A dermatoscopic image of a skin lesion:
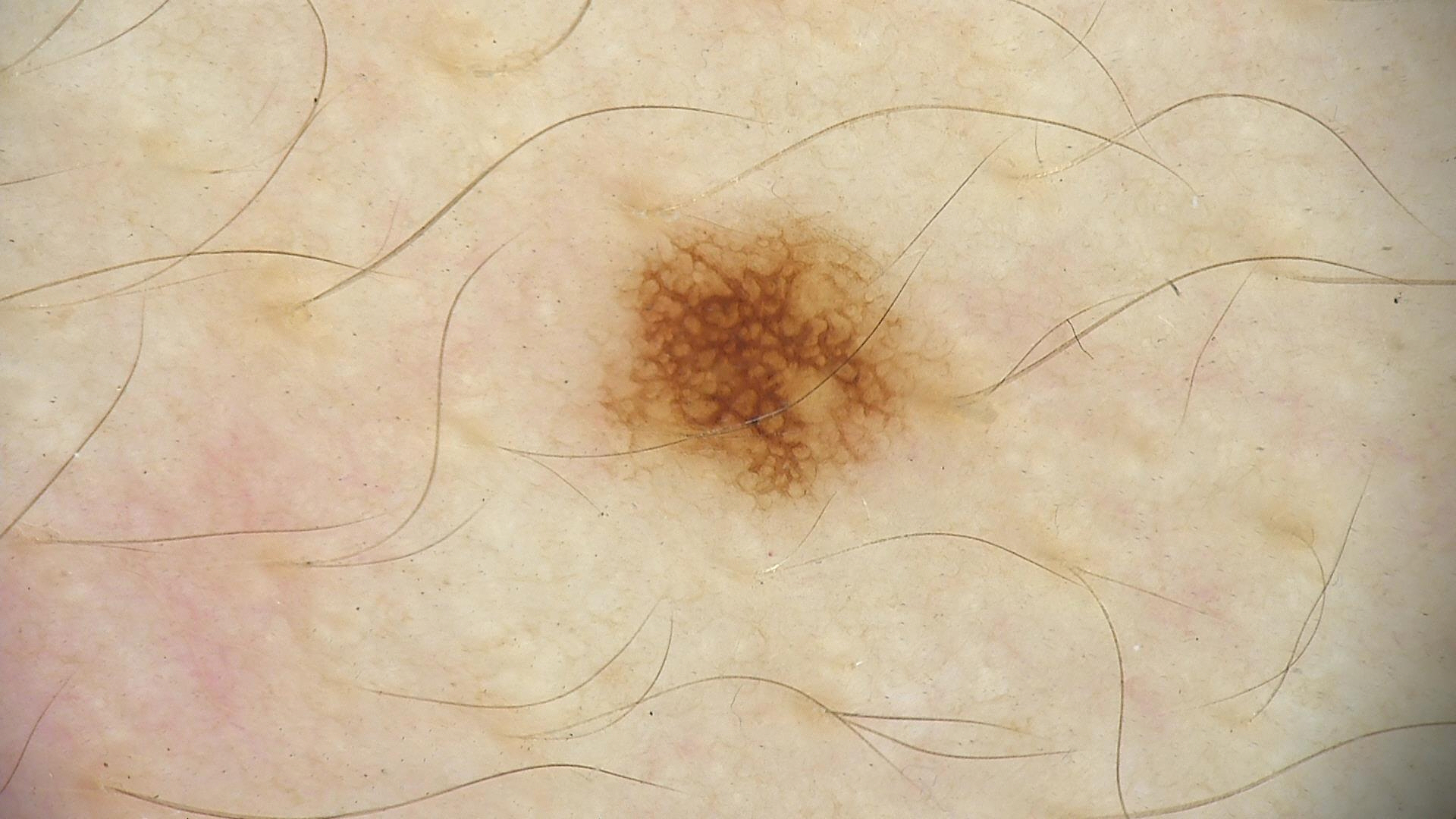The diagnosis was a benign lesion — a dysplastic junctional nevus.